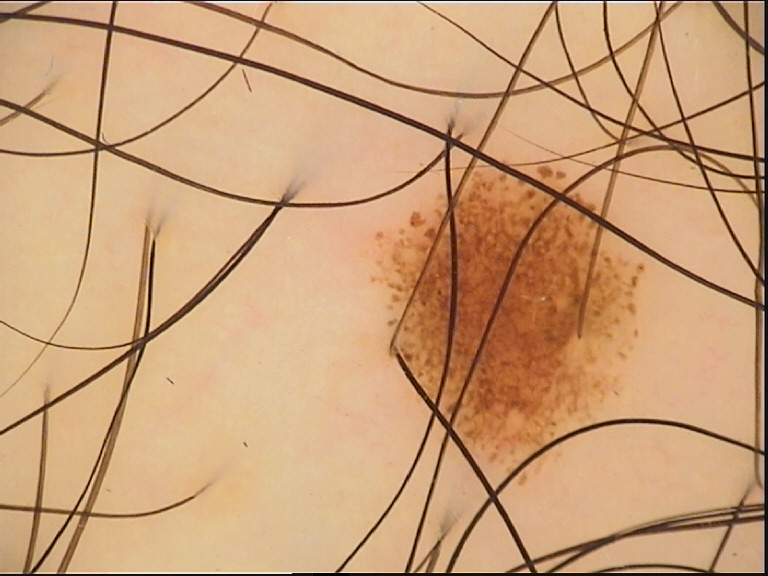diagnostic label: dysplastic junctional nevus (expert consensus).